A dermoscopic image of a skin lesion: 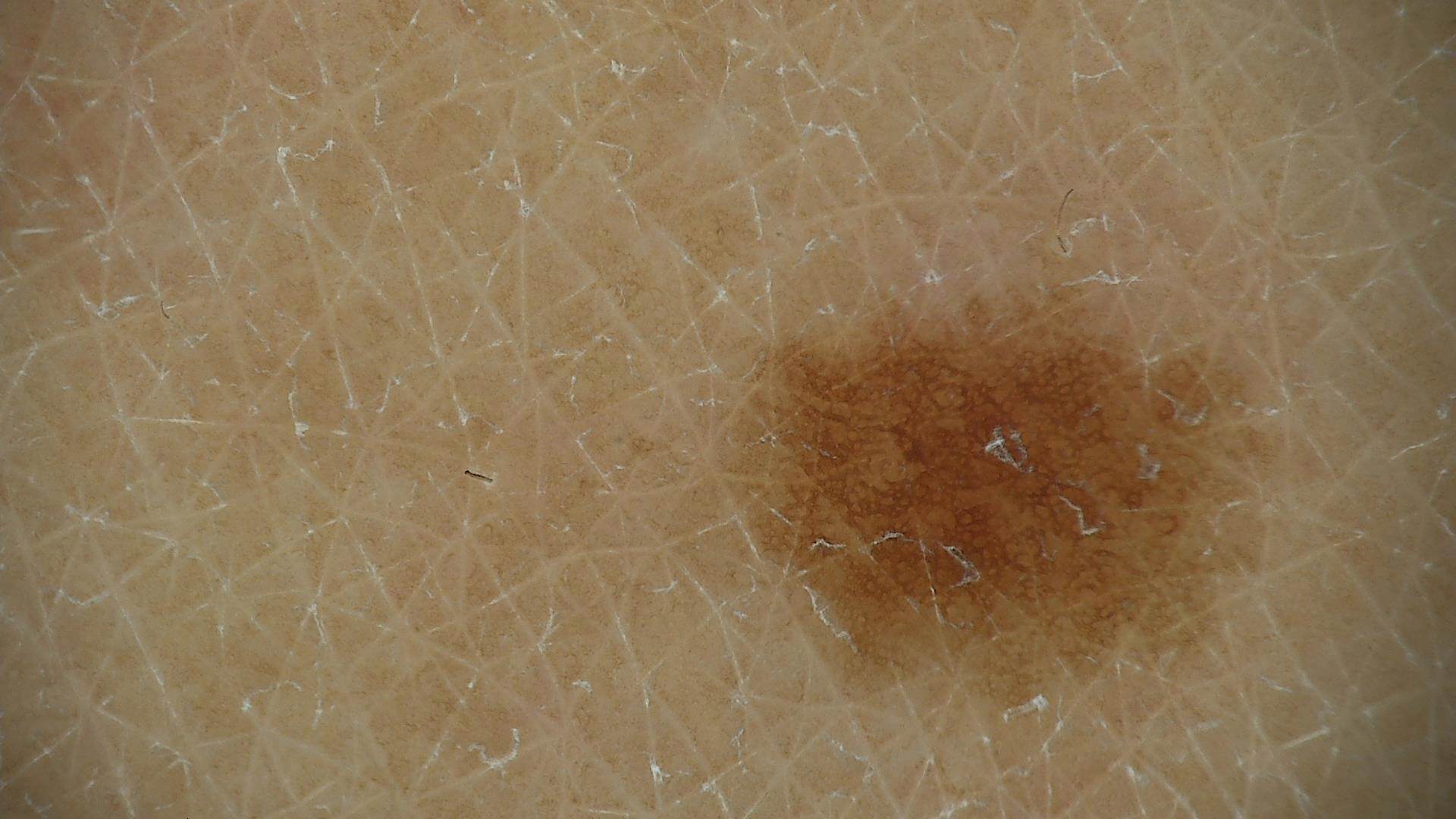The diagnostic label was a banal lesion — a junctional nevus.